Located on the head or neck. Male contributor, age 40–49. This image was taken at an angle:
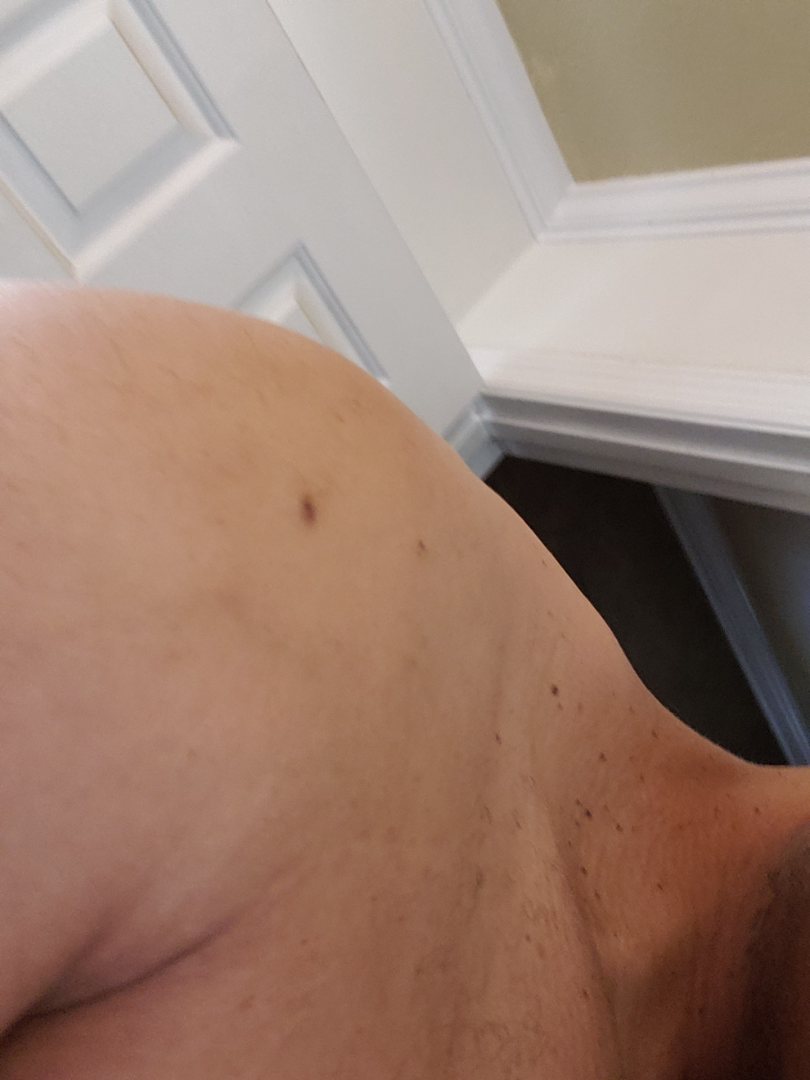Q: Could the case be diagnosed?
A: indeterminate from the photograph
Q: Patient's own categorization?
A: a growth or mole
Q: How does the lesion feel?
A: raised or bumpy
Q: What symptoms does the patient report?
A: bothersome appearance
Q: What is the patient's skin tone?
A: FST IV; lay reviewers estimated Monk Skin Tone 3 or 4
Q: When did this start?
A: more than five years